The patient says their skin reddens painfully with sun exposure · a moderate number of moles by the patient's own estimate · a female patient age 50 · a dermatoscopic image of a skin lesion · imaged for a research study, with no referral diagnosis recorded — 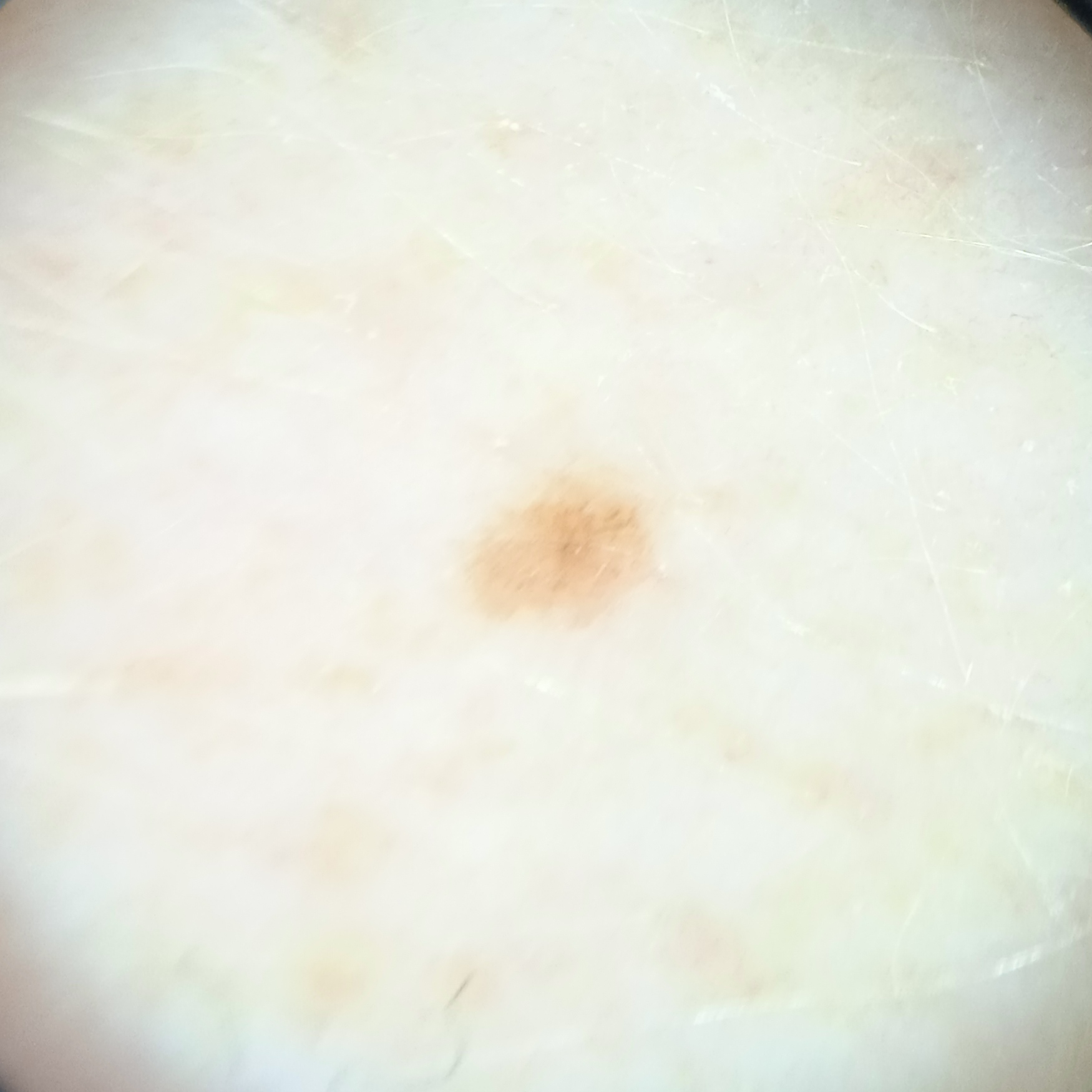anatomic site: an arm
size: 2 mm
assessment: melanocytic nevus (dermatologist consensus)